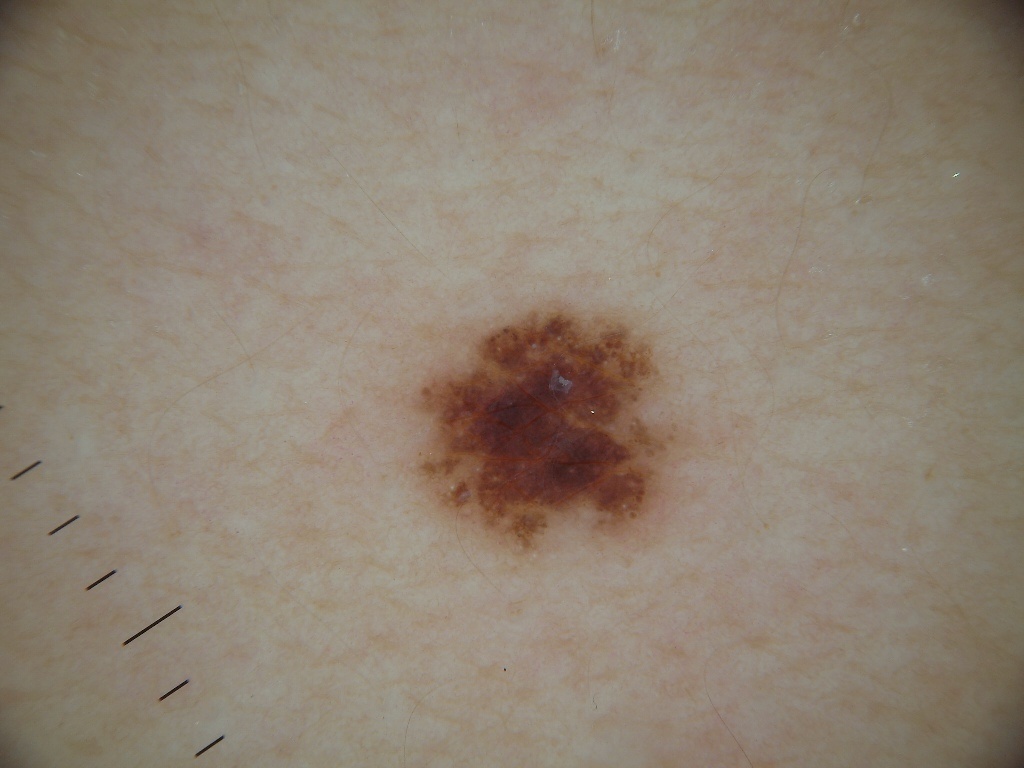This is a dermoscopic photograph of a skin lesion.
A female subject, aged approximately 25.
The dermoscopic pattern shows no globules, pigment network, milia-like cysts, negative network, or streaks.
As (left, top, right, bottom), the lesion spans 411 305 686 552.
Consistent with a melanocytic nevus, a benign skin lesion.